Per the chart, no melanoma in first-degree relatives and no previous melanoma · a dermoscopic image of a skin lesion · a female patient roughly 25 years of age · the patient is FST II — 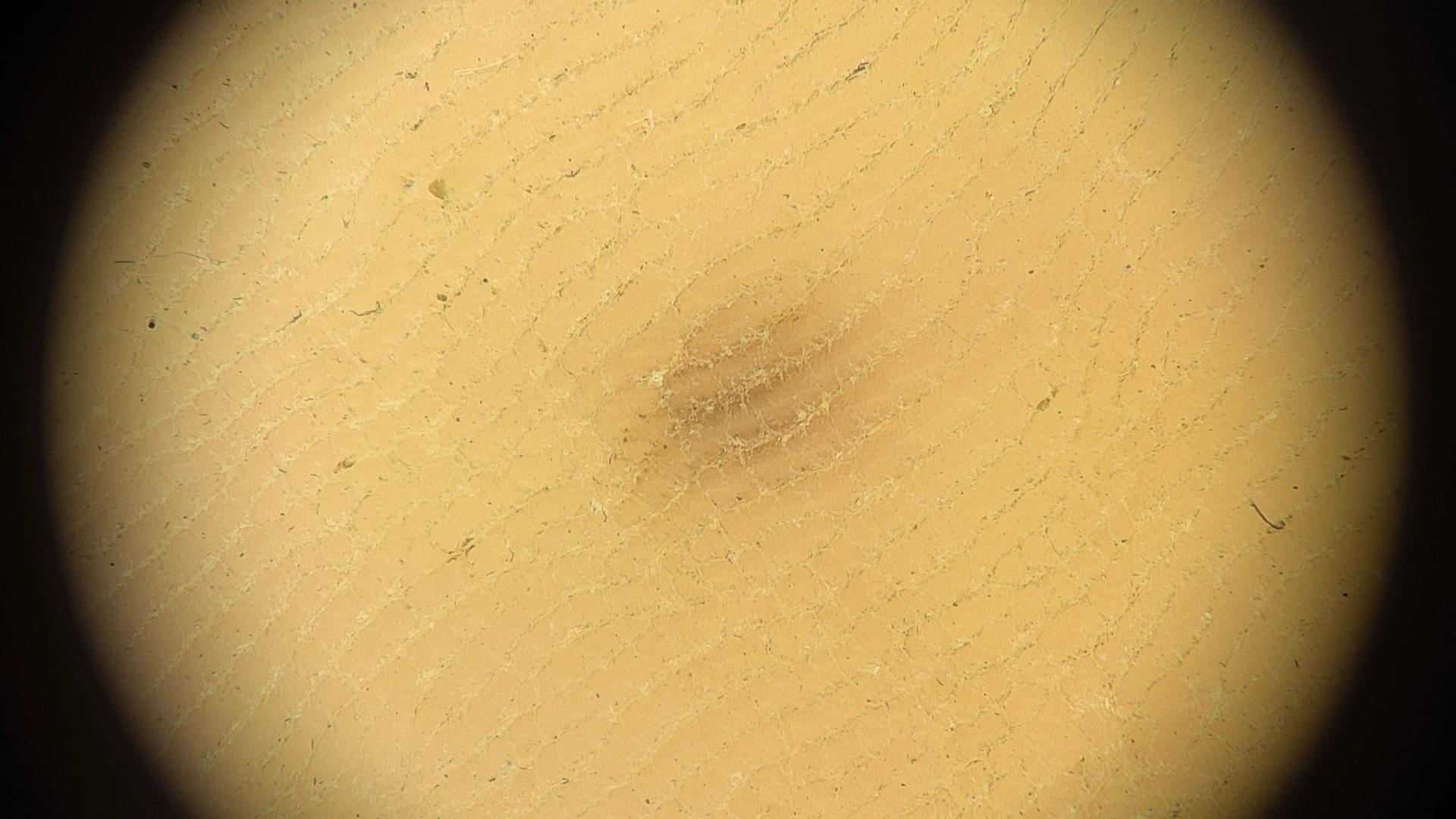Located on a lower extremity.
Expert review favored a nevus.